A dermoscopic image of a skin lesion. A male patient aged around 75 — 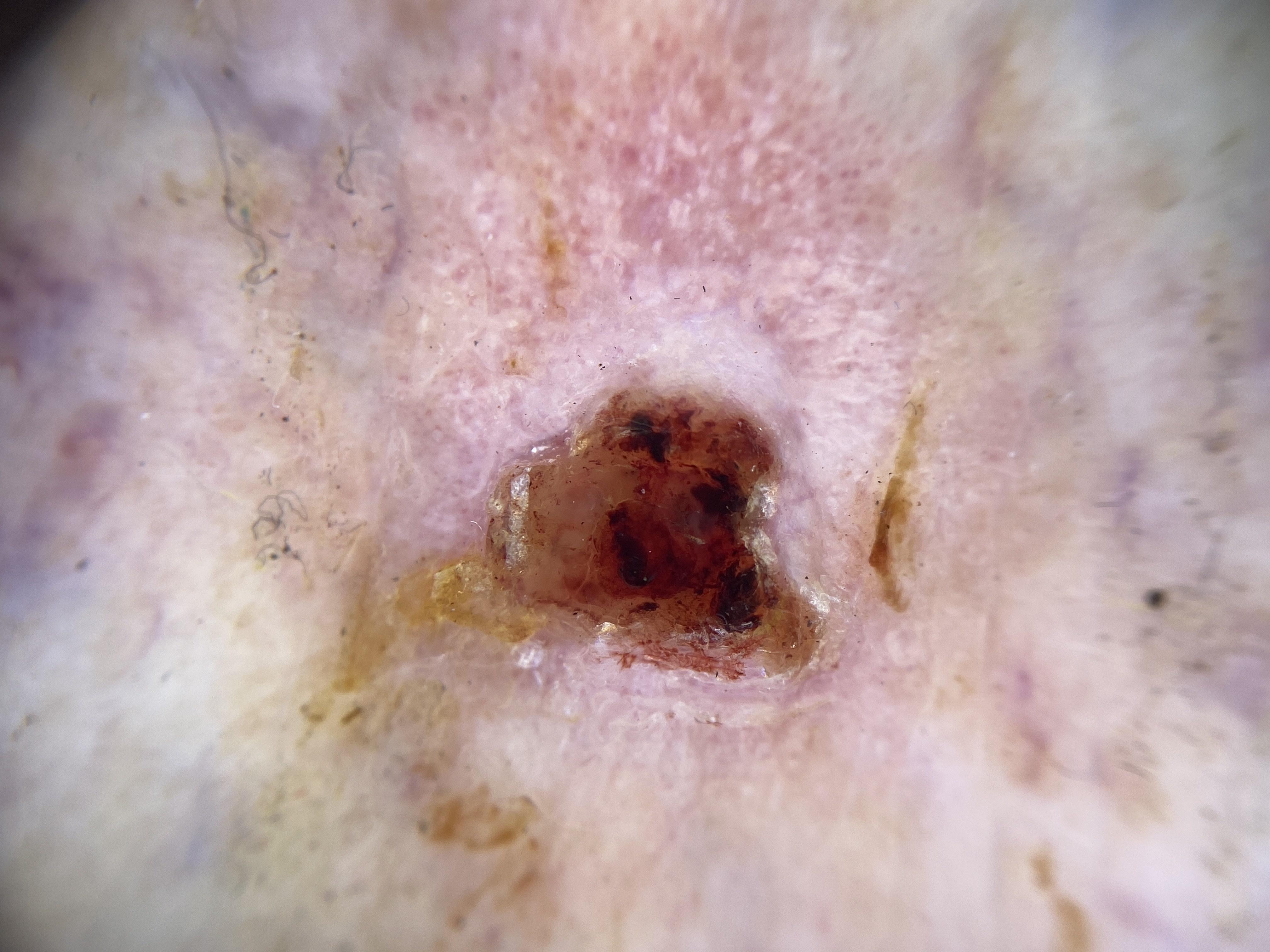Case:
- body site — a lower extremity
- diagnosis — Basal cell carcinoma (biopsy-proven)